A dermatoscopic image of a skin lesion.
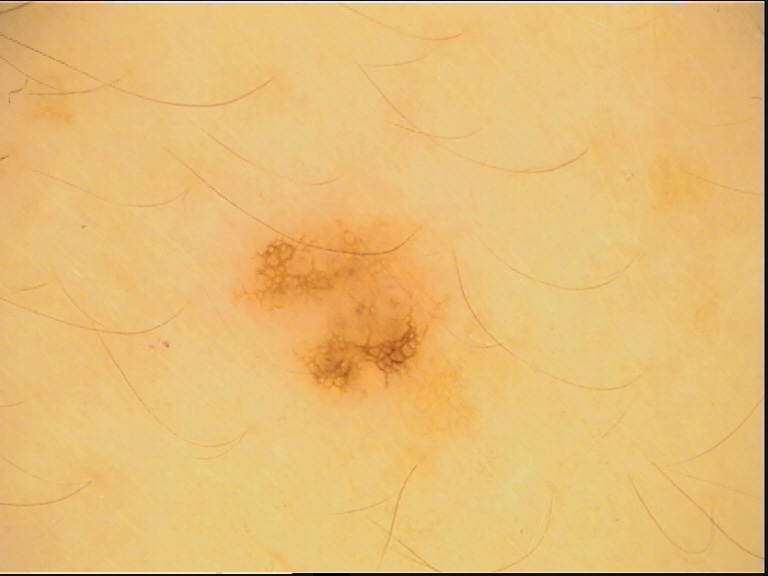| feature | finding |
|---|---|
| diagnostic label | dysplastic junctional nevus (expert consensus) |